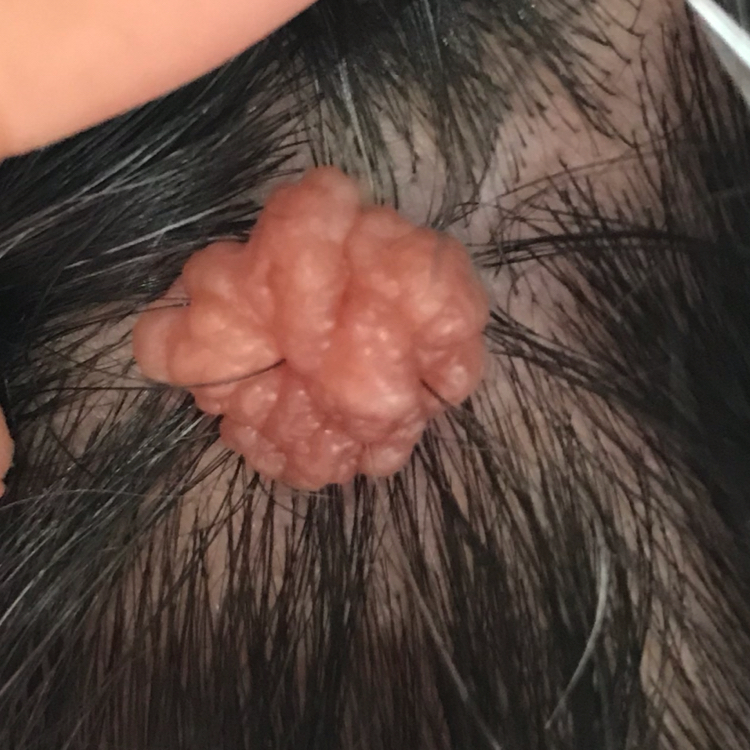Findings: A subject aged 55. The lesion involves the scalp. Conclusion: Expert review favored a nevus.